Texture is reported as flat. Human graders estimated Monk Skin Tone 2. The leg is involved. The photograph was taken at an angle. The contributor notes the condition has been present for less than one week: 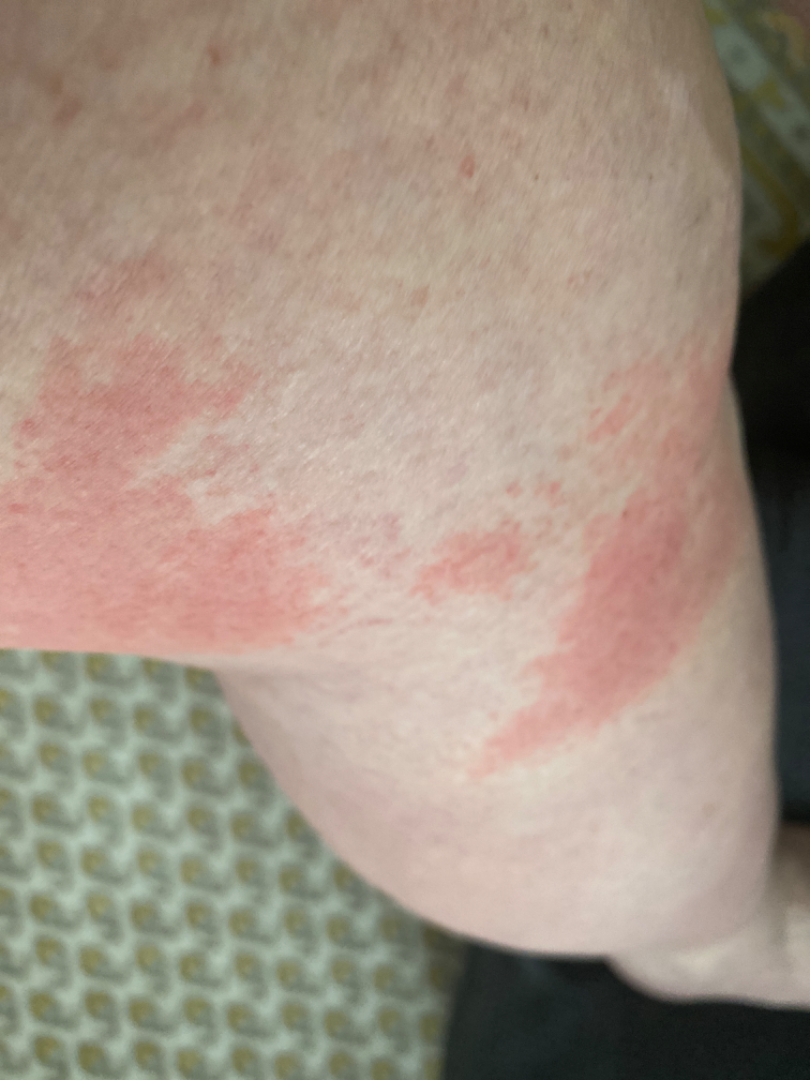assessment = favoring Hypersensitivity